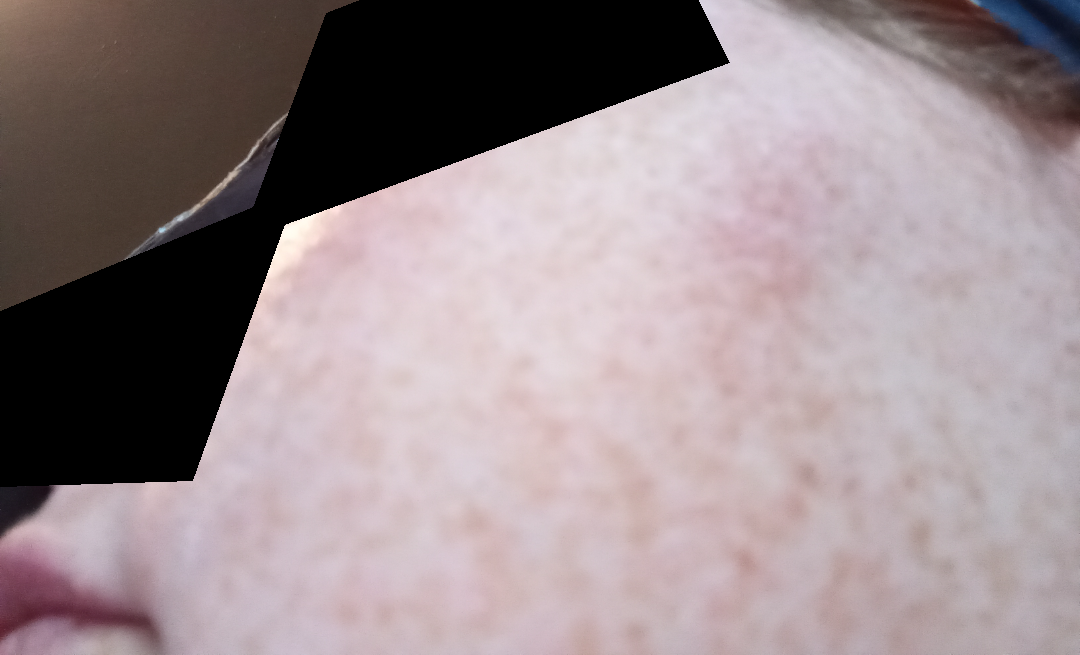Findings:
The impression on review was Rosacea.